A dermoscopic close-up of a skin lesion.
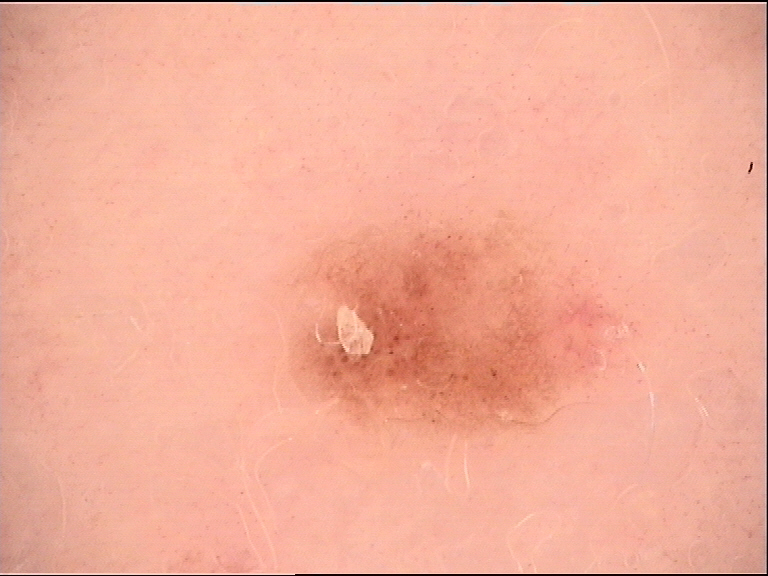Impression:
The diagnosis was a benign lesion — a dysplastic junctional nevus.